A female subject aged 49 · a clinical photograph of a skin lesion · the patient was assessed as FST III · by history, prior malignancy (patient or family) and prior skin cancer (patient or family) — 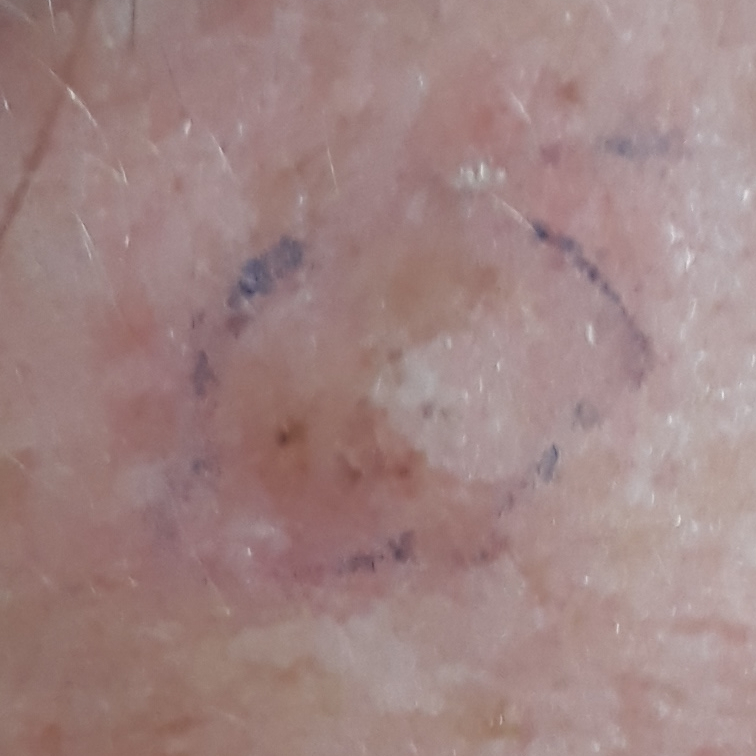site — the face; diameter — 10 × 10 mm; patient-reported symptoms — elevation; pathology — basal cell carcinoma (biopsy-proven).